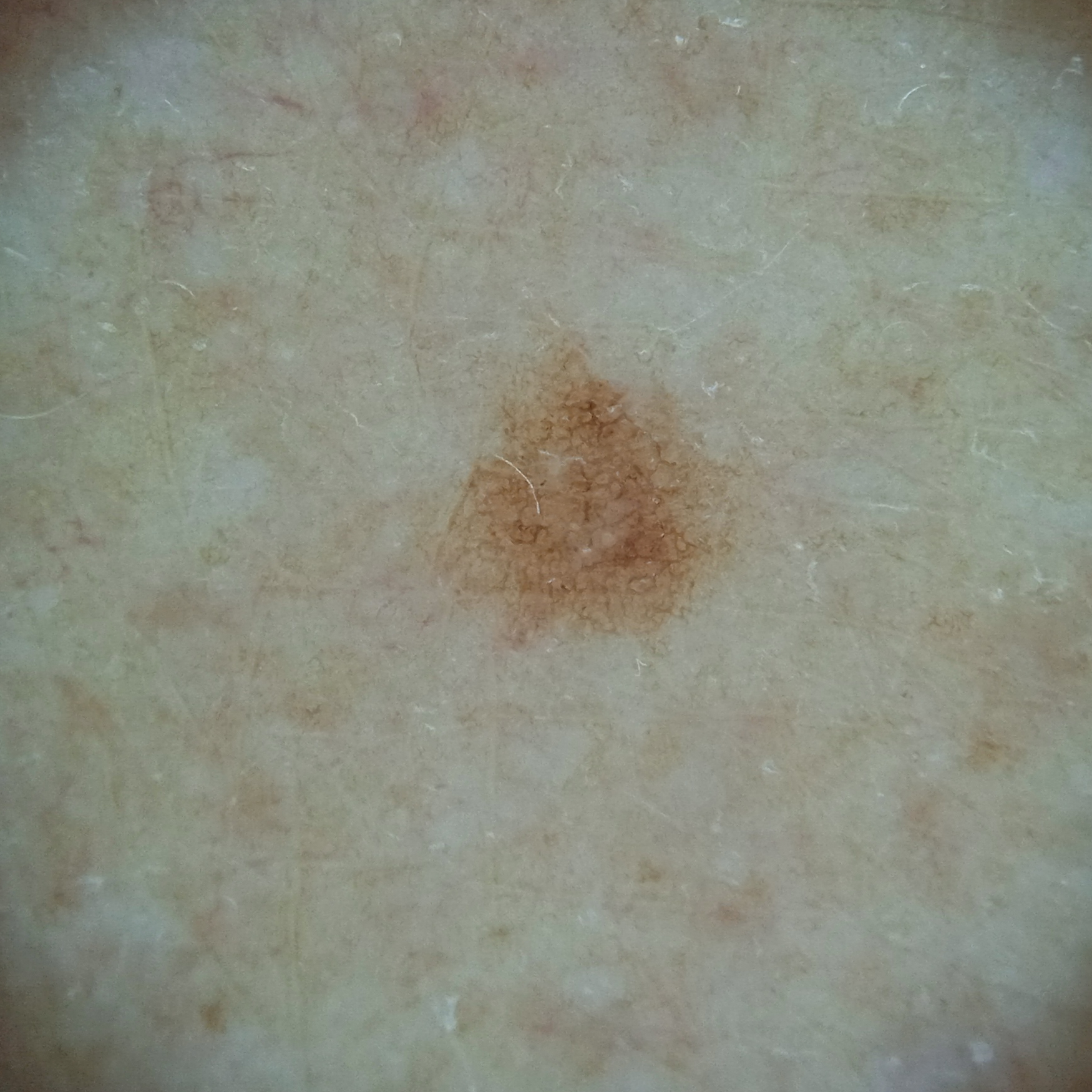Clinical context:
Imaged for a research study, with no referral diagnosis recorded. A skin lesion imaged with a dermatoscope. The lesion is on an arm.
Conclusion:
The lesion was assessed as a melanocytic nevus.